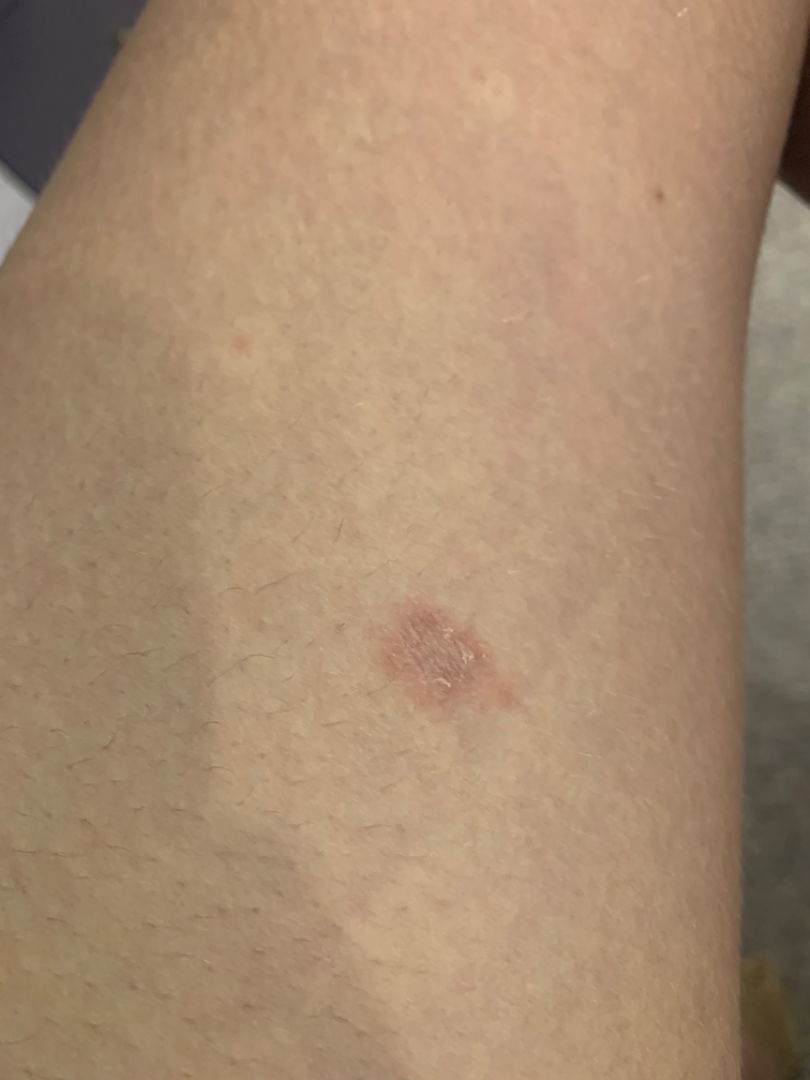A close-up photograph. In keeping with Eczema.